A dermoscopic close-up of a skin lesion:
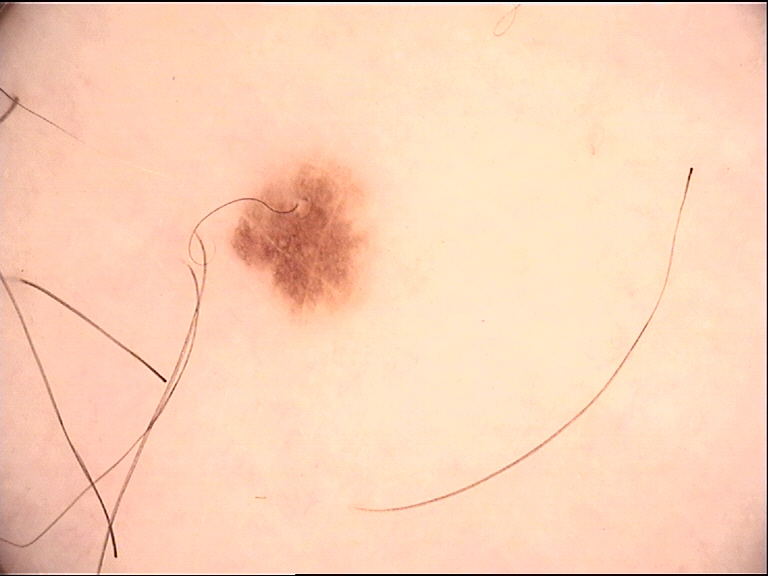Conclusion: Classified as a benign lesion — a dysplastic junctional nevus.